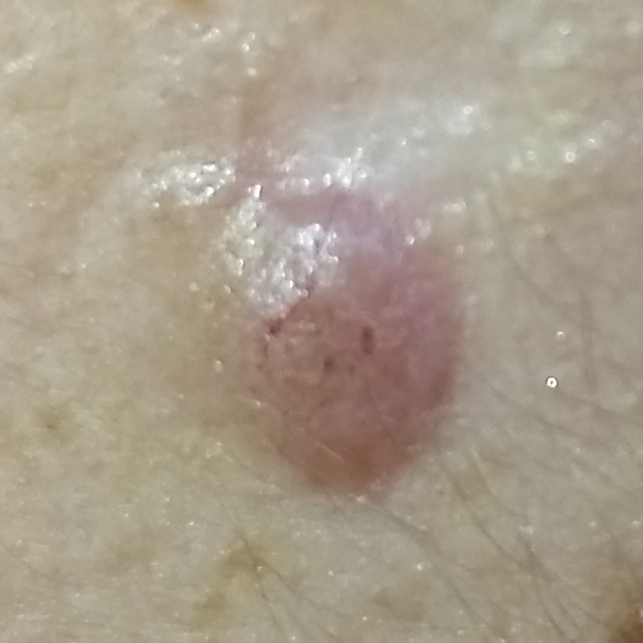Case summary: A clinical photograph of a skin lesion. Located on the face. Conclusion: The biopsy diagnosis was a basal cell carcinoma.